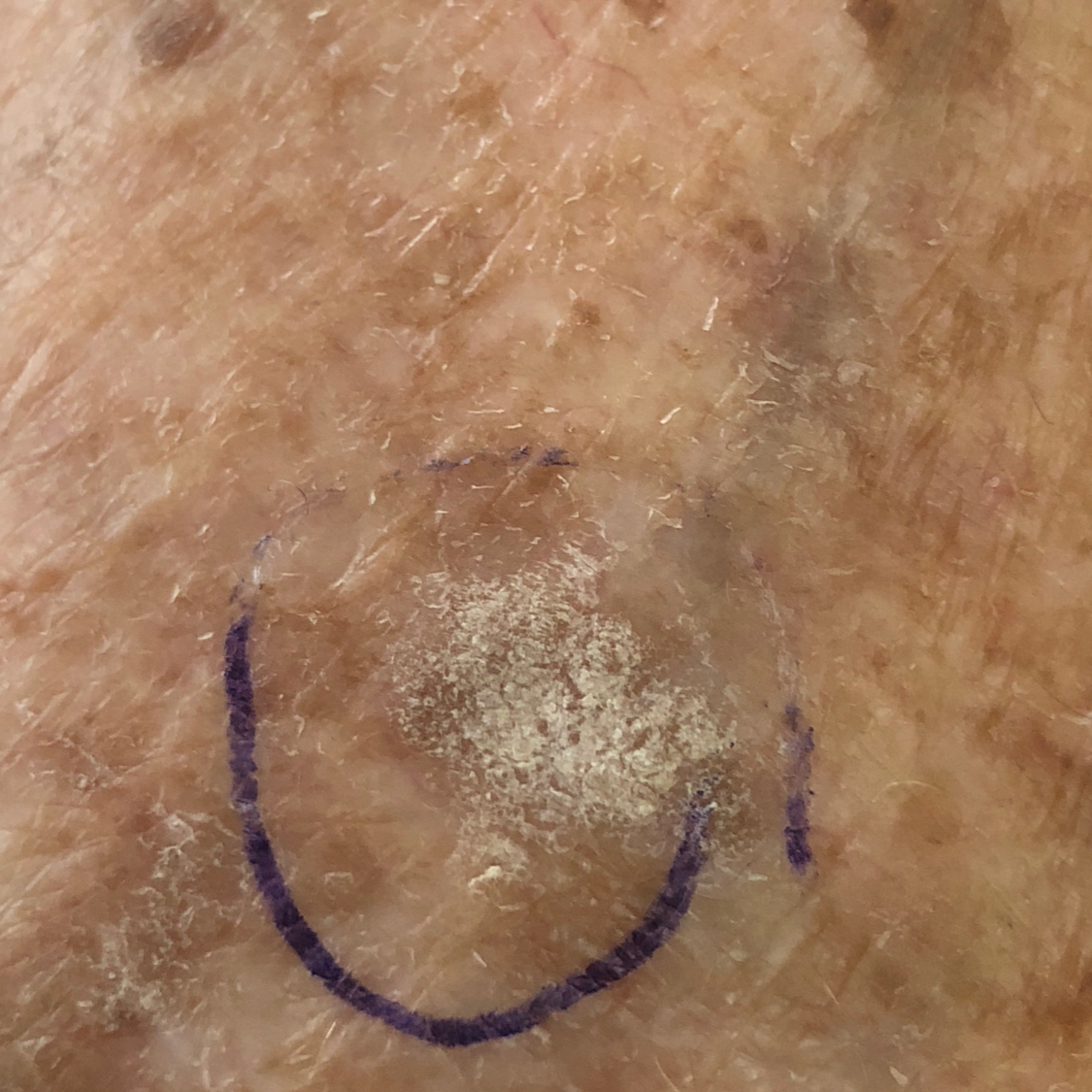A patient in their late 70s.
A clinical close-up photograph of a skin lesion.
The lesion involves a forearm.
By the patient's account, the lesion itches, but does not hurt and has not bled.
Expert review favored a lesion of indeterminate malignant potential — an actinic keratosis.